The photograph is a close-up of the affected area · the patient is a female aged 30–39 — 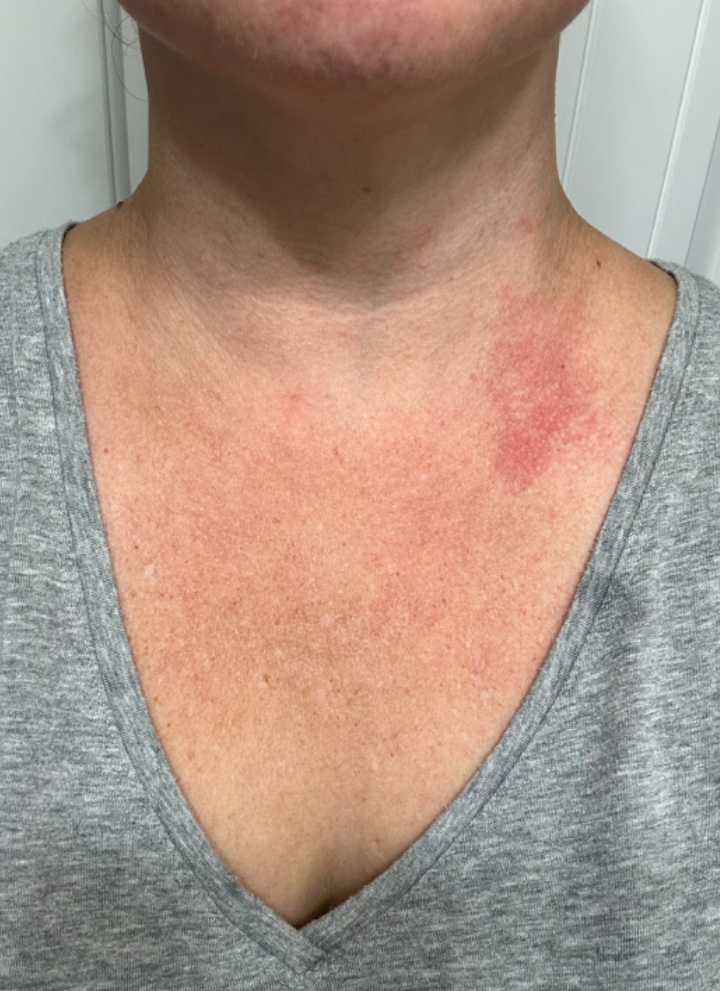The lesion is described as flat and raised or bumpy.
Reported duration is about one day.
No associated lesion symptoms were reported.
On photographic review by a dermatologist: Berloque dermatitis, Allergic Contact Dermatitis and Irritant Contact Dermatitis were each considered, in no particular order.